This is a close-up image.
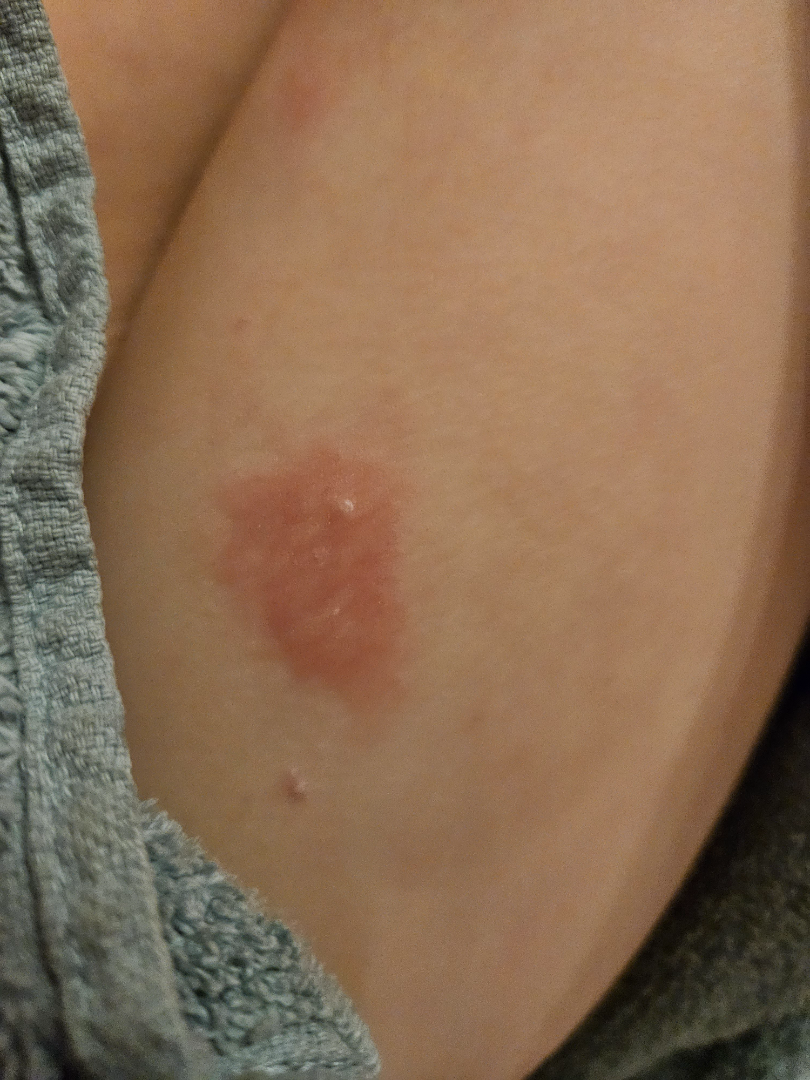assessment=most likely Eczema; also raised was Impetigo